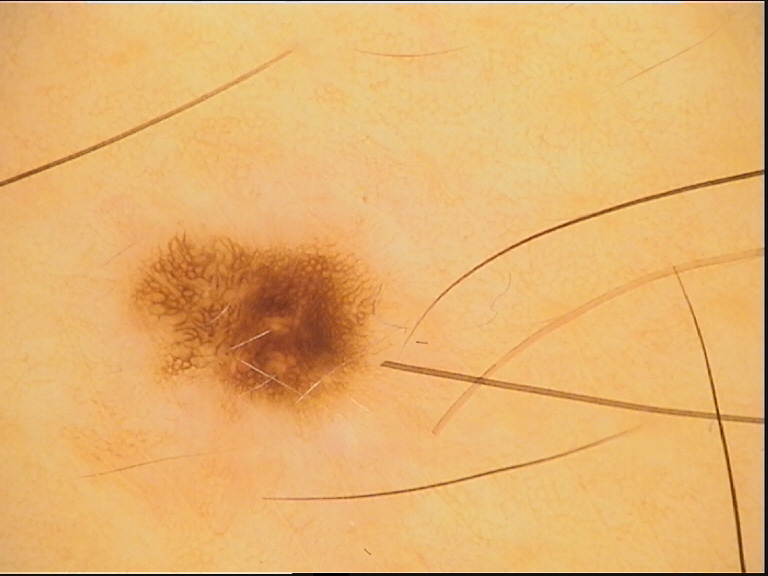Impression:
The diagnostic label was a junctional nevus.